Located on the leg; the contributor is a female aged 18–29; this is a close-up image.
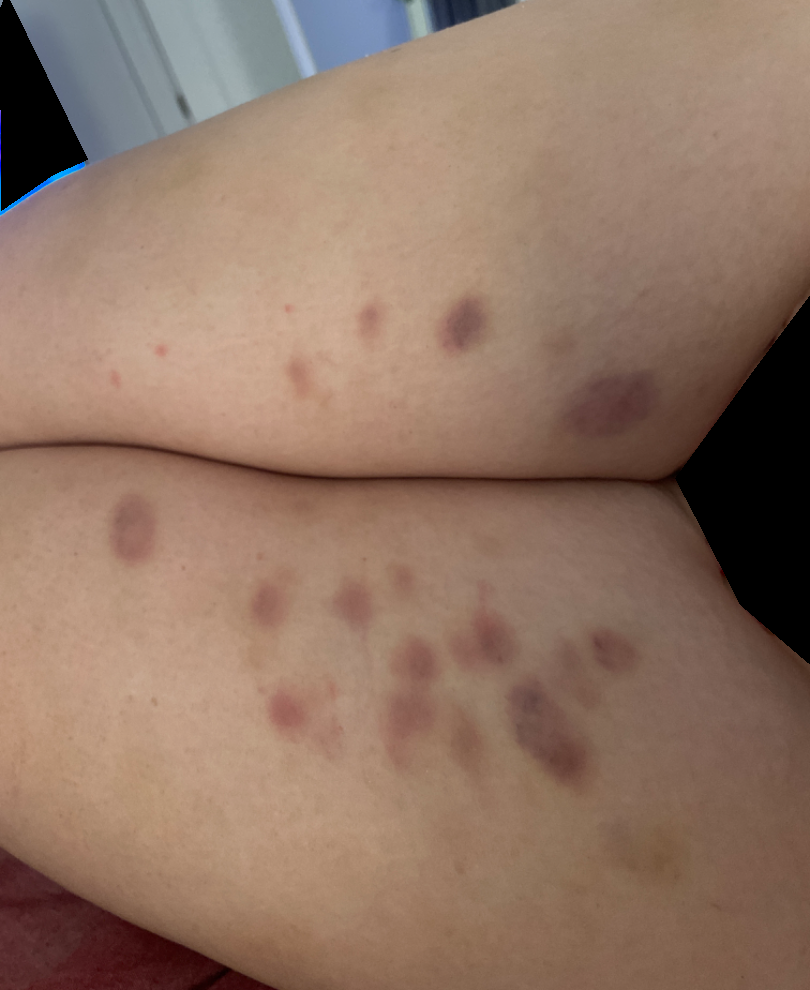On teledermatology review: ecchymoses (most likely).